A skin lesion imaged with a dermatoscope:
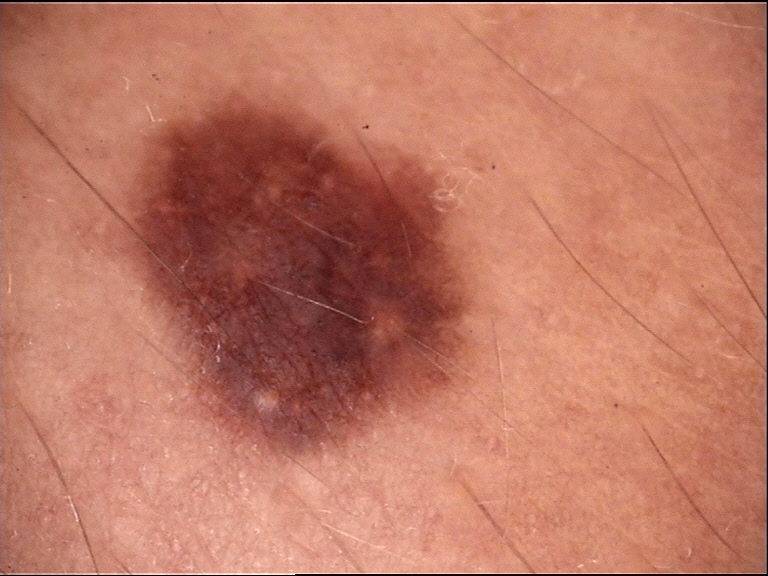Conclusion: Labeled as a dysplastic junctional nevus.